A skin lesion imaged with a dermatoscope:
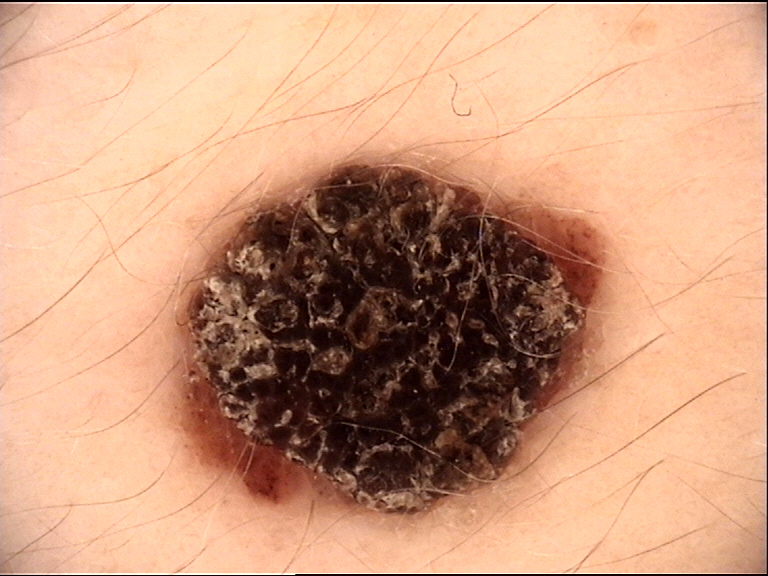class: congenital compound nevus (expert consensus).